The photograph was taken at a distance · no associated systemic symptoms reported · the lesion is associated with bothersome appearance and pain · present for less than one week: 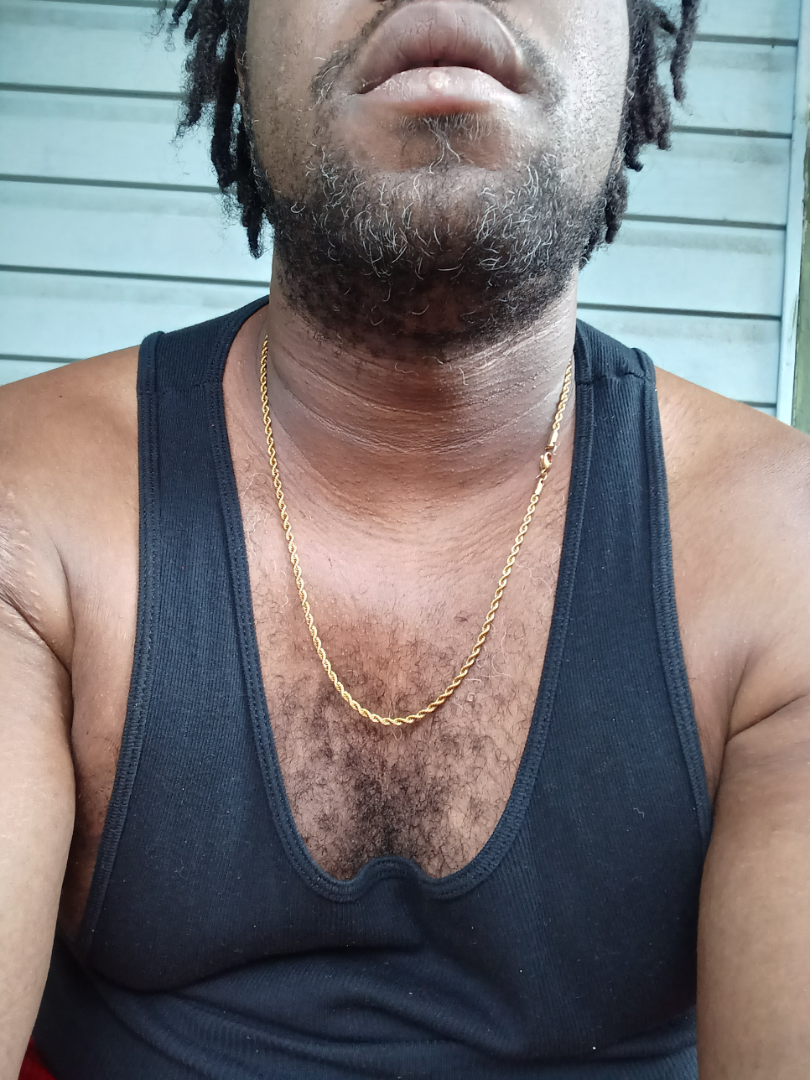No discernible skin pathology was identified on dermatologist review.